This is a close-up image:
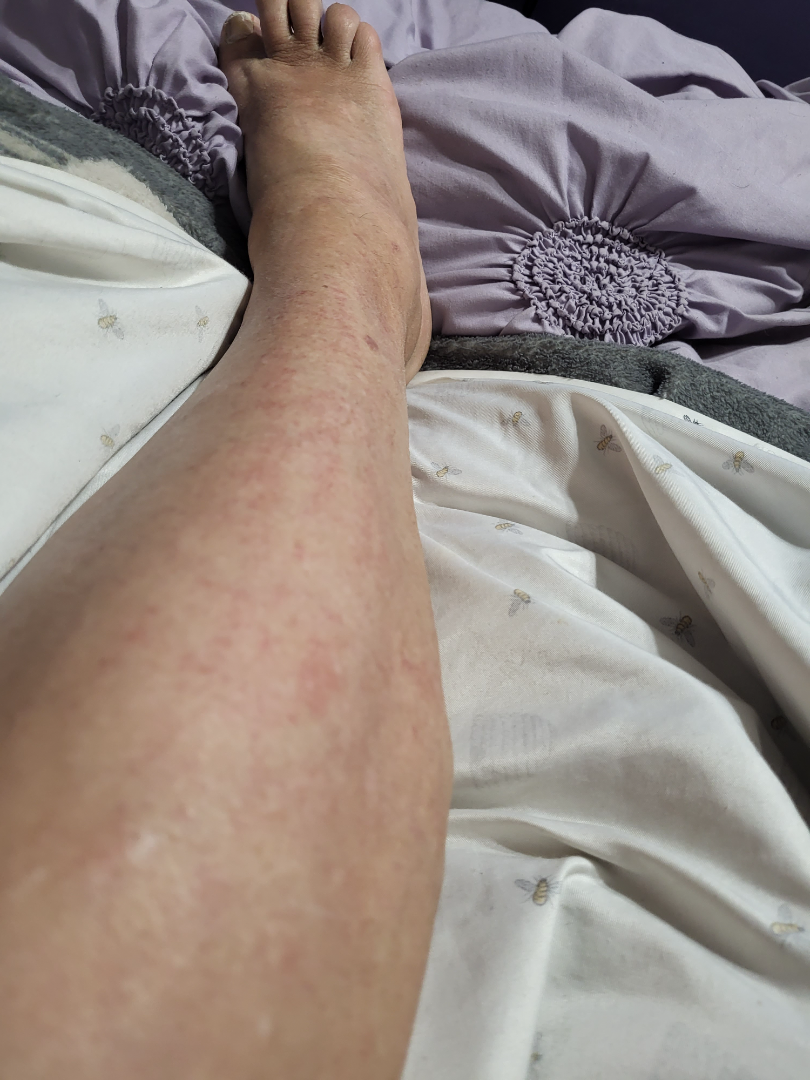The case was difficult to assess from the available photograph.